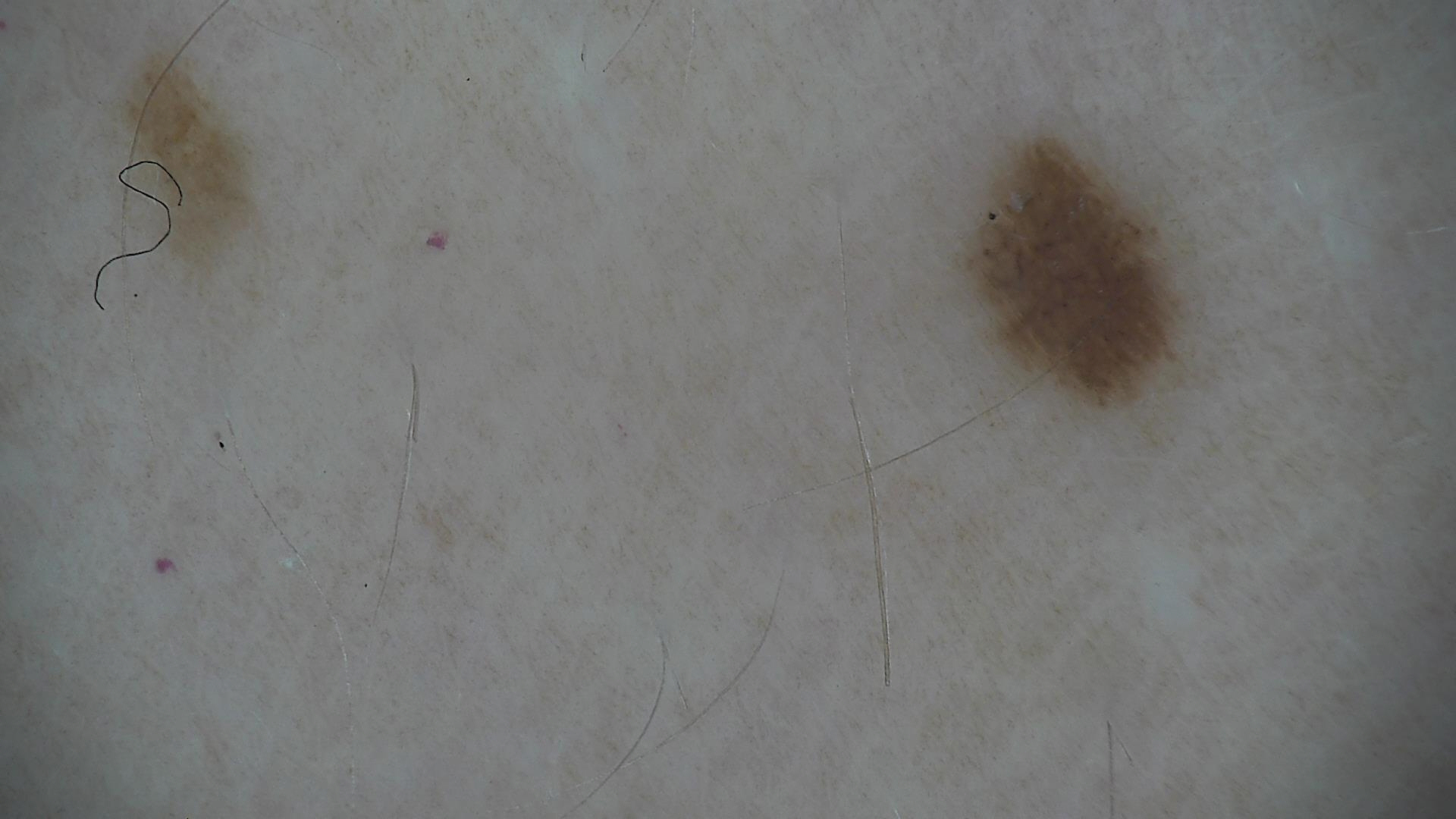Case:
- image type — dermoscopy
- diagnostic label — dysplastic junctional nevus (expert consensus)